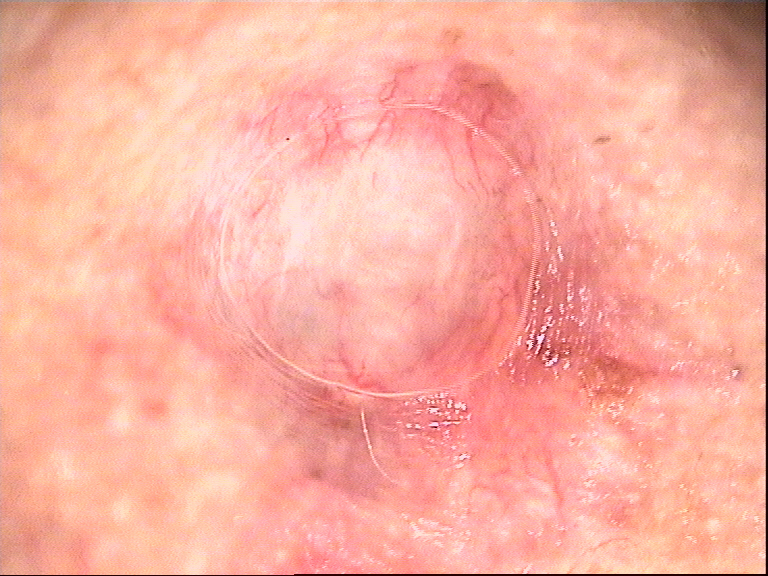A dermoscopic photograph of a skin lesion. Biopsy-confirmed as a keratinocytic, malignant lesion — a basal cell carcinoma.